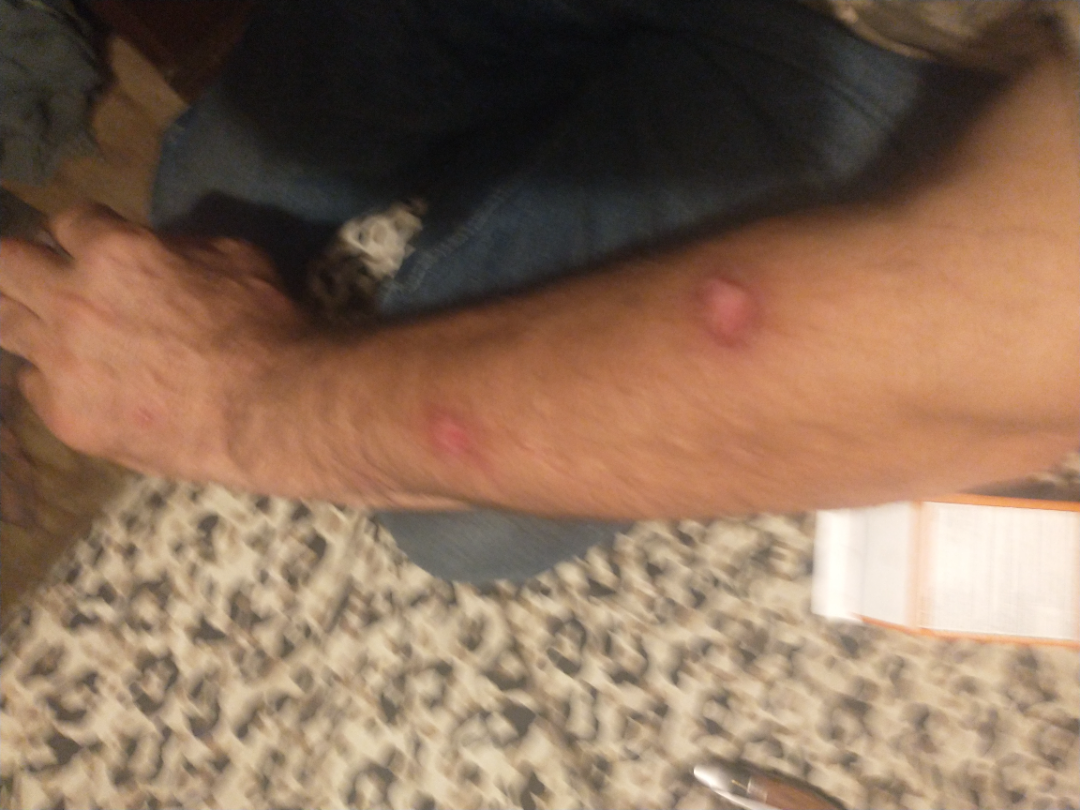This image was taken at a distance. The leg and arm are involved. Lay reviewers estimated Monk Skin Tone 6 (US pool) or 4 (India pool). Male contributor, age 40–49. Associated systemic symptoms include fatigue. The condition has been present for three to twelve months. On remote dermatologist review: consistent with Scar Condition.